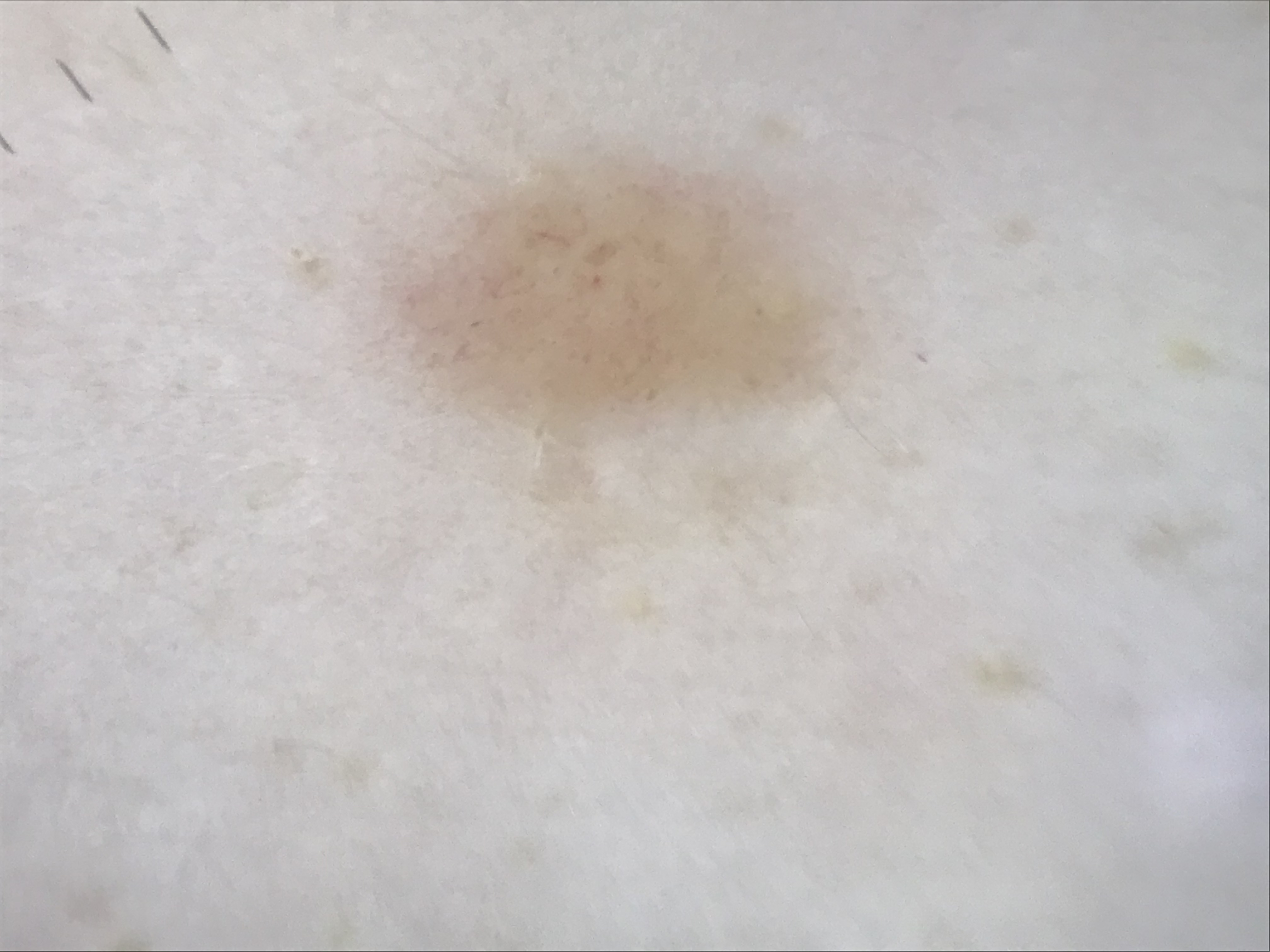{"diagnosis": {"name": "junctional nevus", "code": "jb", "malignancy": "benign", "super_class": "melanocytic", "confirmation": "expert consensus"}}